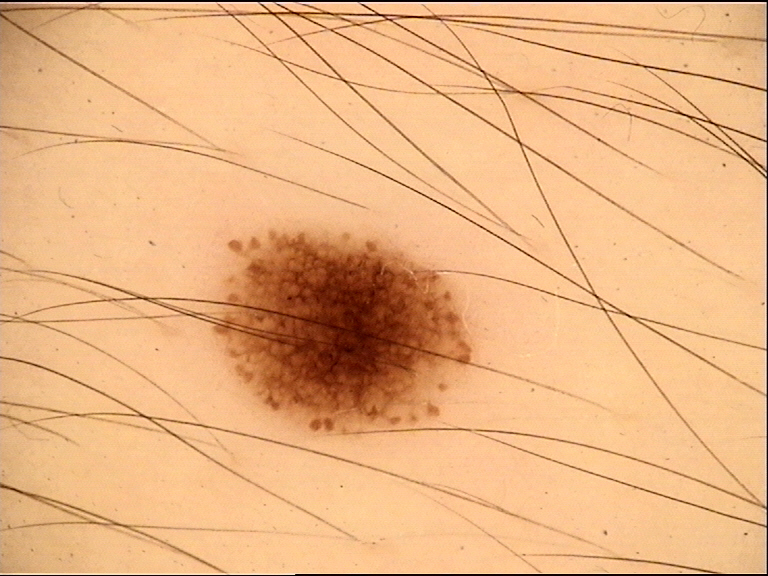image — dermatoscopy; label — dysplastic junctional nevus (expert consensus).